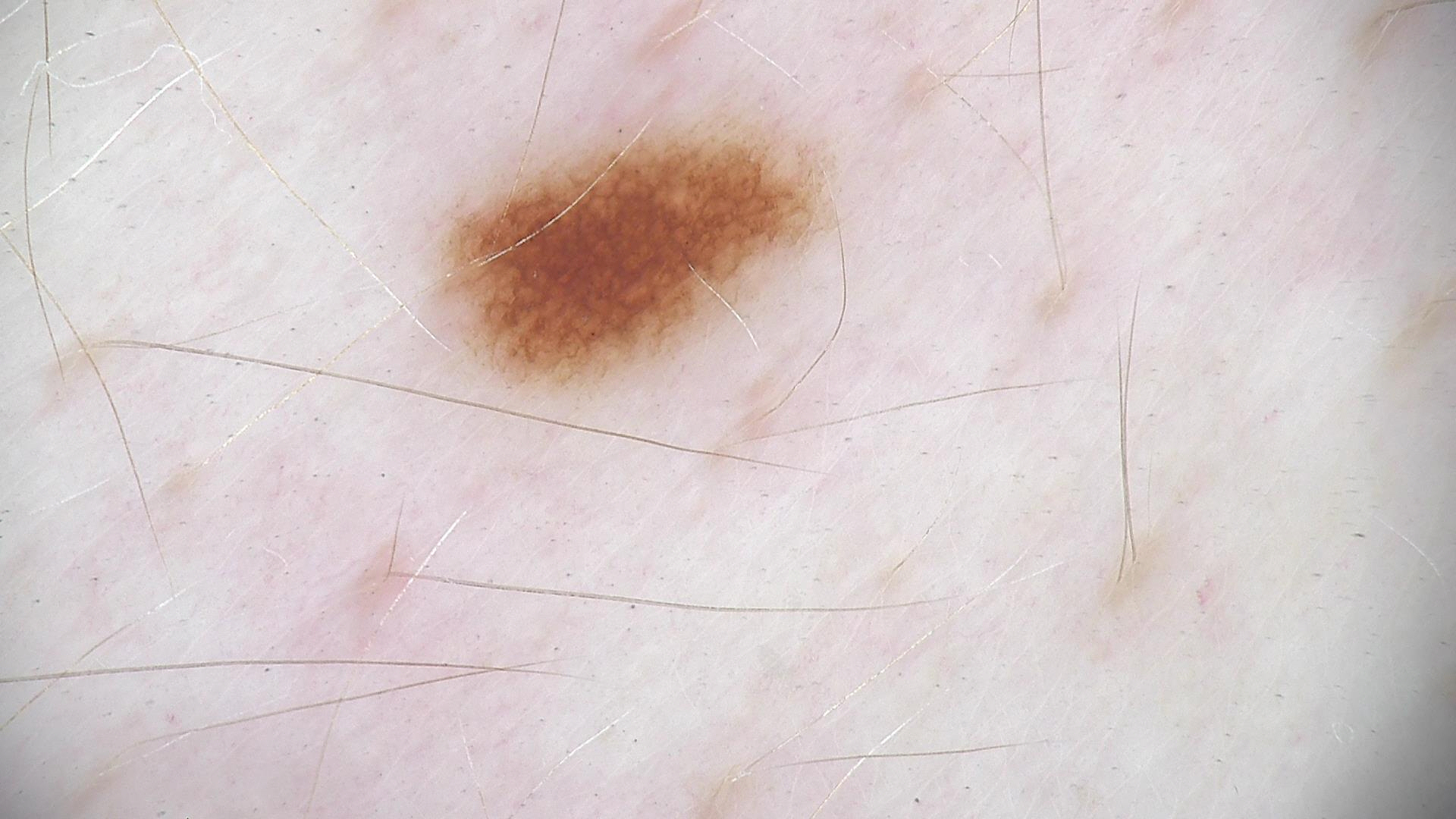Diagnosed as a dysplastic junctional nevus.